A smartphone photograph of a skin lesion · a subject 48 years of age: 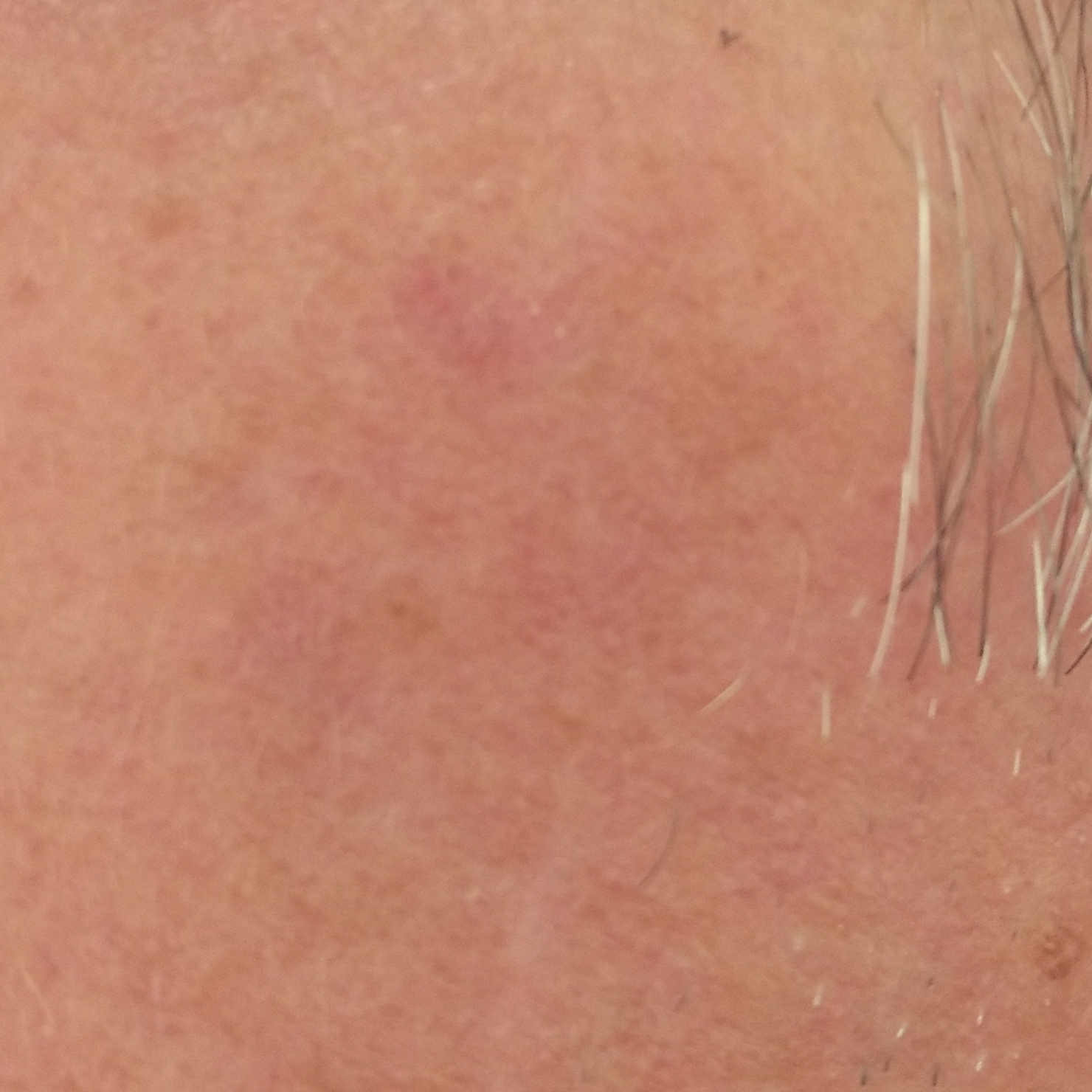Q: What is the diagnosis?
A: actinic keratosis (clinical consensus)